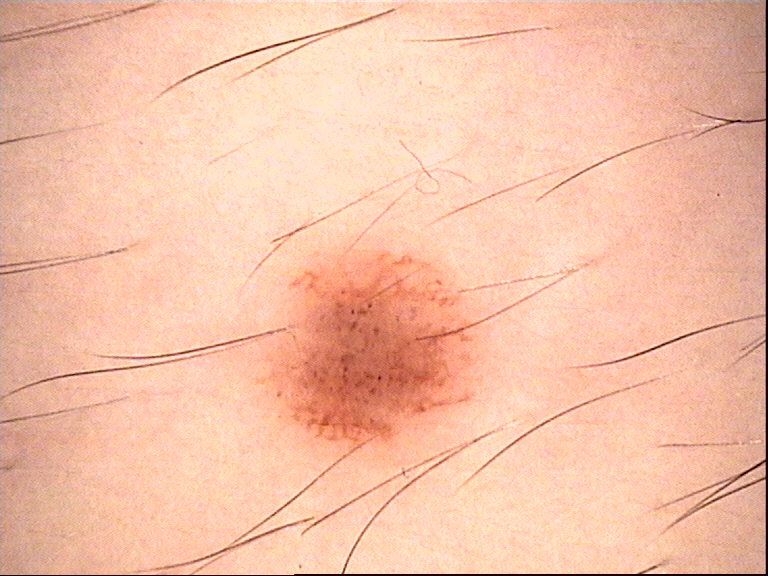image type: dermatoscopy | class: dysplastic junctional nevus (expert consensus).